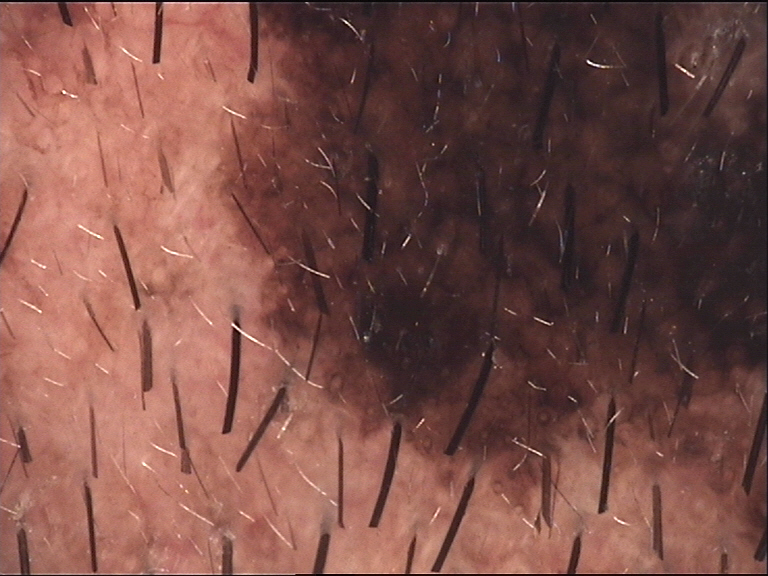Summary: This is a banal lesion. Impression: Consistent with a congenital compound nevus.